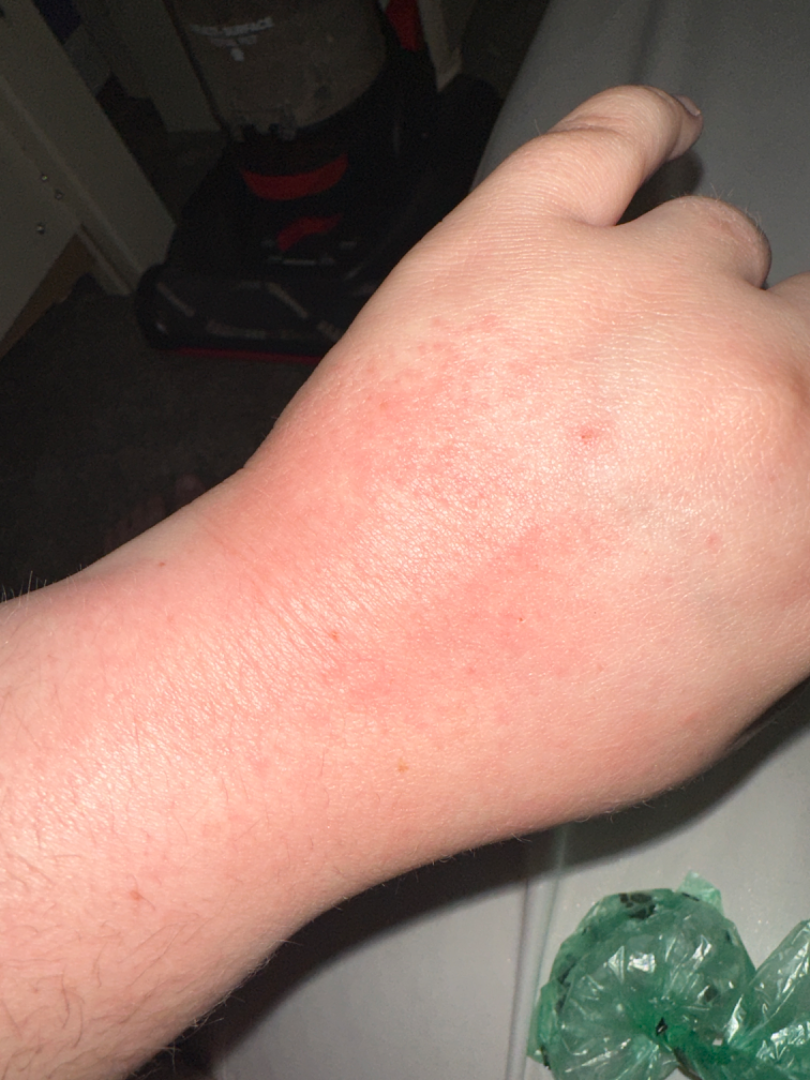Findings:
The skin findings could not be characterized from the image.